The photograph is a close-up of the affected area; the affected area is the back of the hand, palm, head or neck, back of the torso, arm and front of the torso — 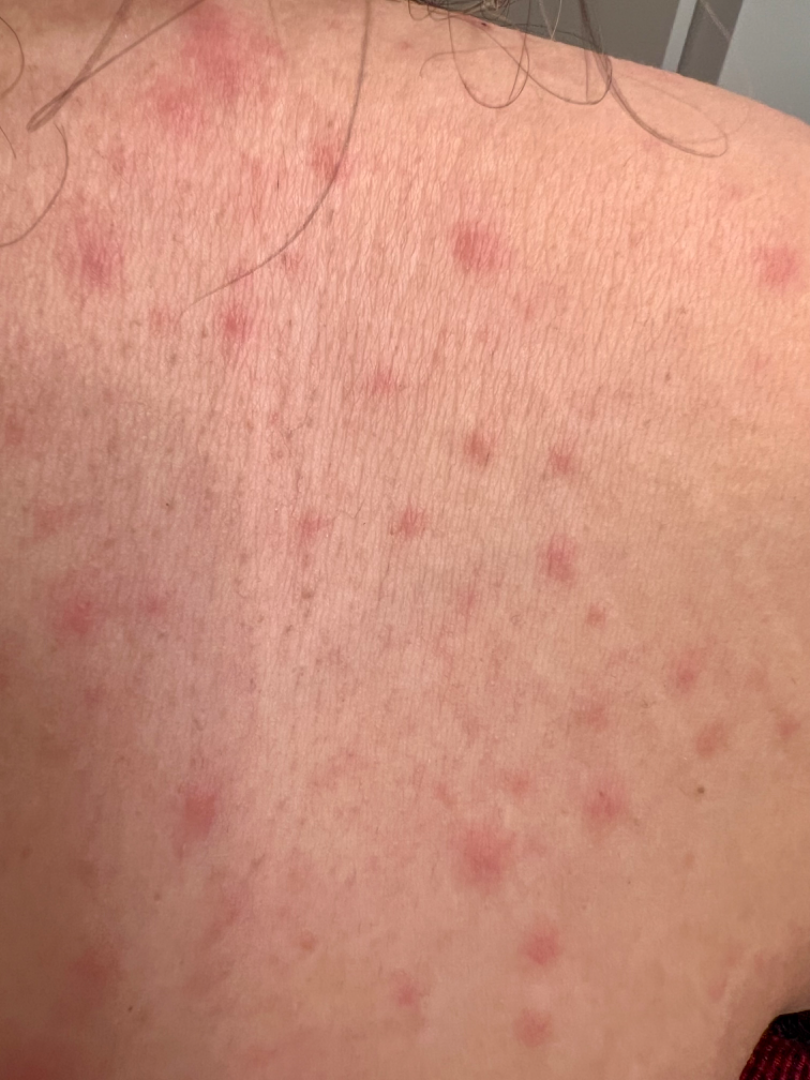The dermatologist could not determine a likely condition from the photograph alone. The patient reports itching and burning. Present for about one day.